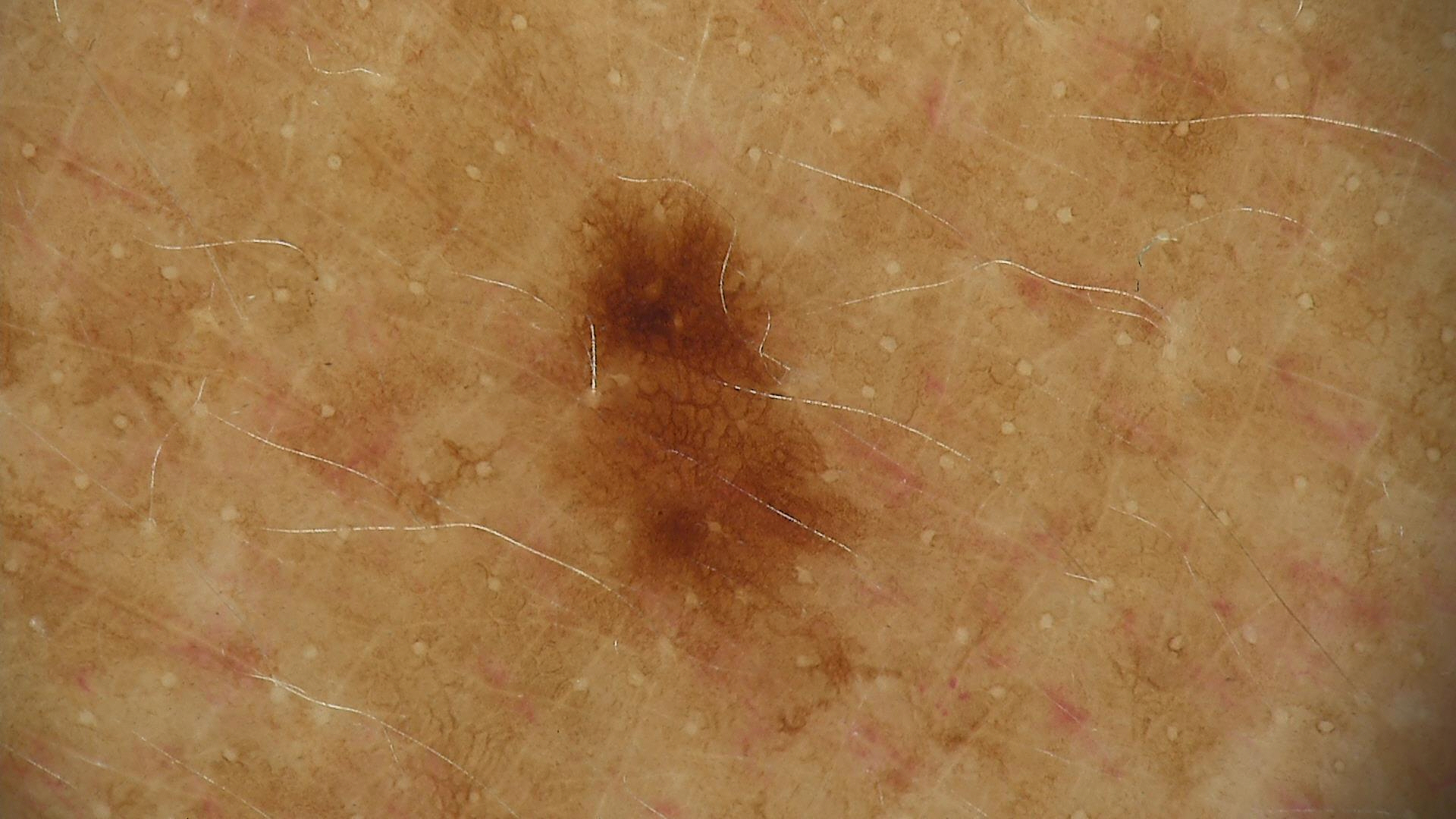Findings:
A dermoscopic photograph of a skin lesion.
Impression:
Consistent with a benign lesion — a dysplastic junctional nevus.